A male patient 89 years old · the patient says their skin reddens painfully with sun exposure · referred for assessment of suspected basal cell carcinoma:
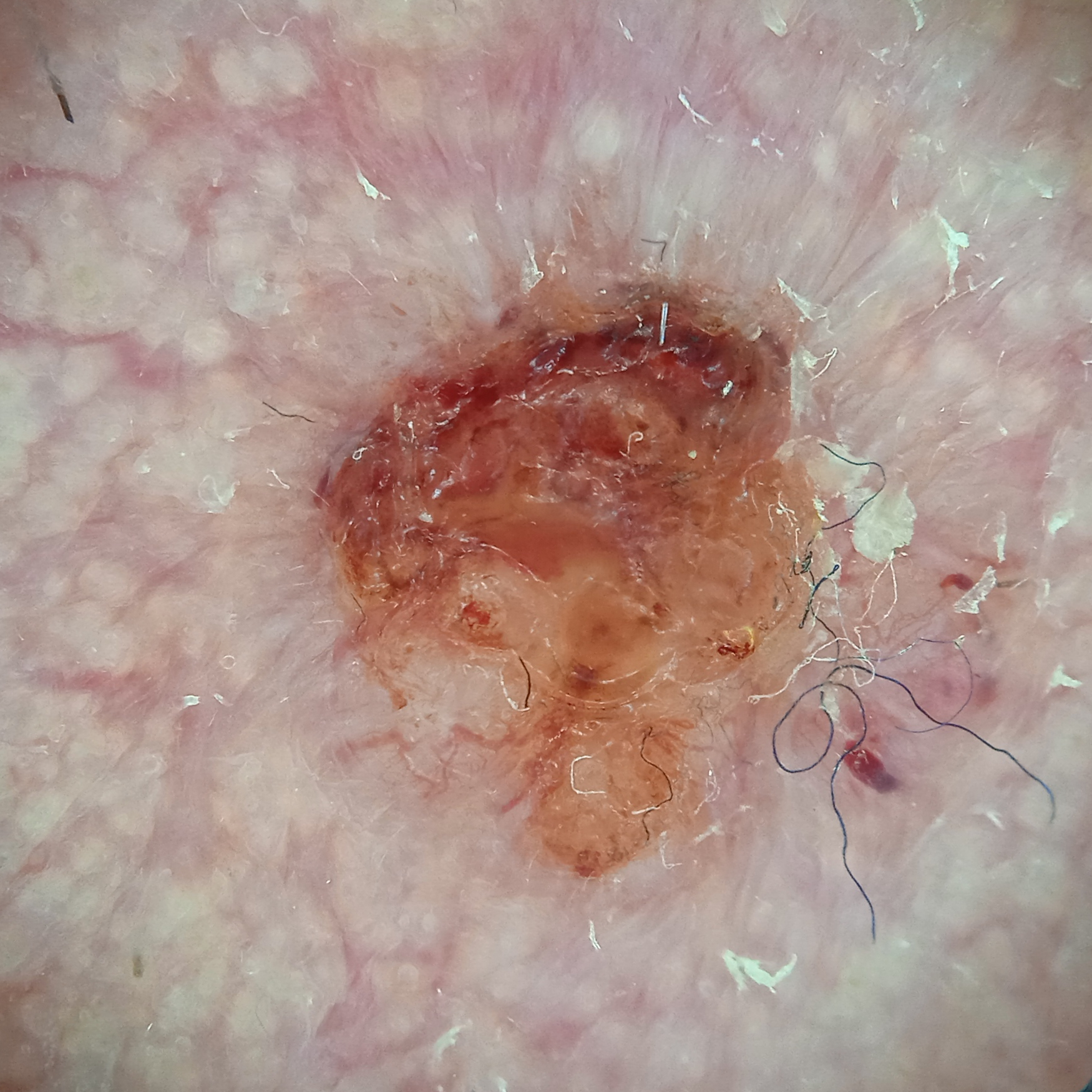Q: Where is the lesion?
A: the face
Q: What did the biopsy show?
A: basal cell carcinoma (biopsy-proven)